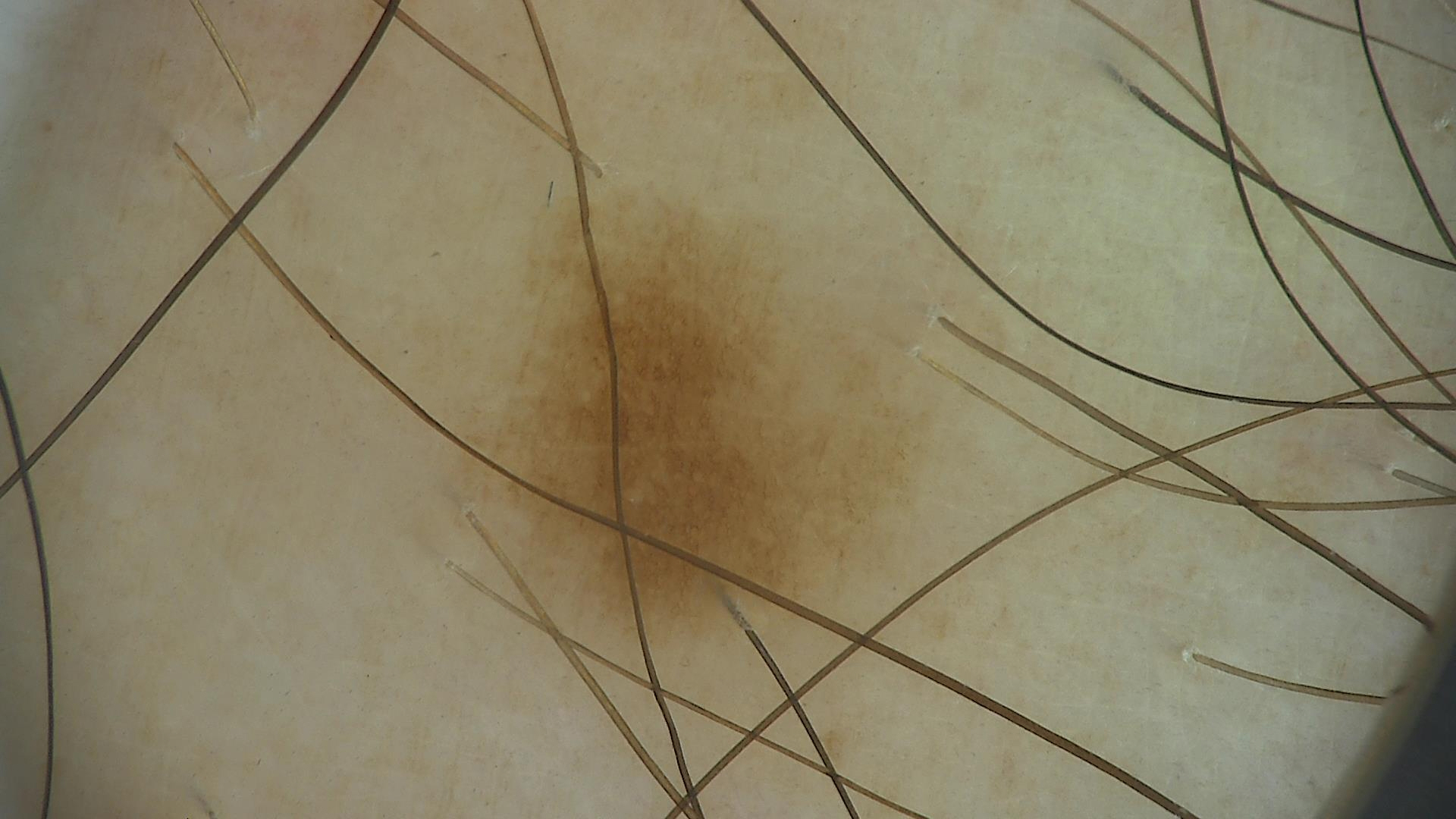diagnosis: lentigo simplex (expert consensus).